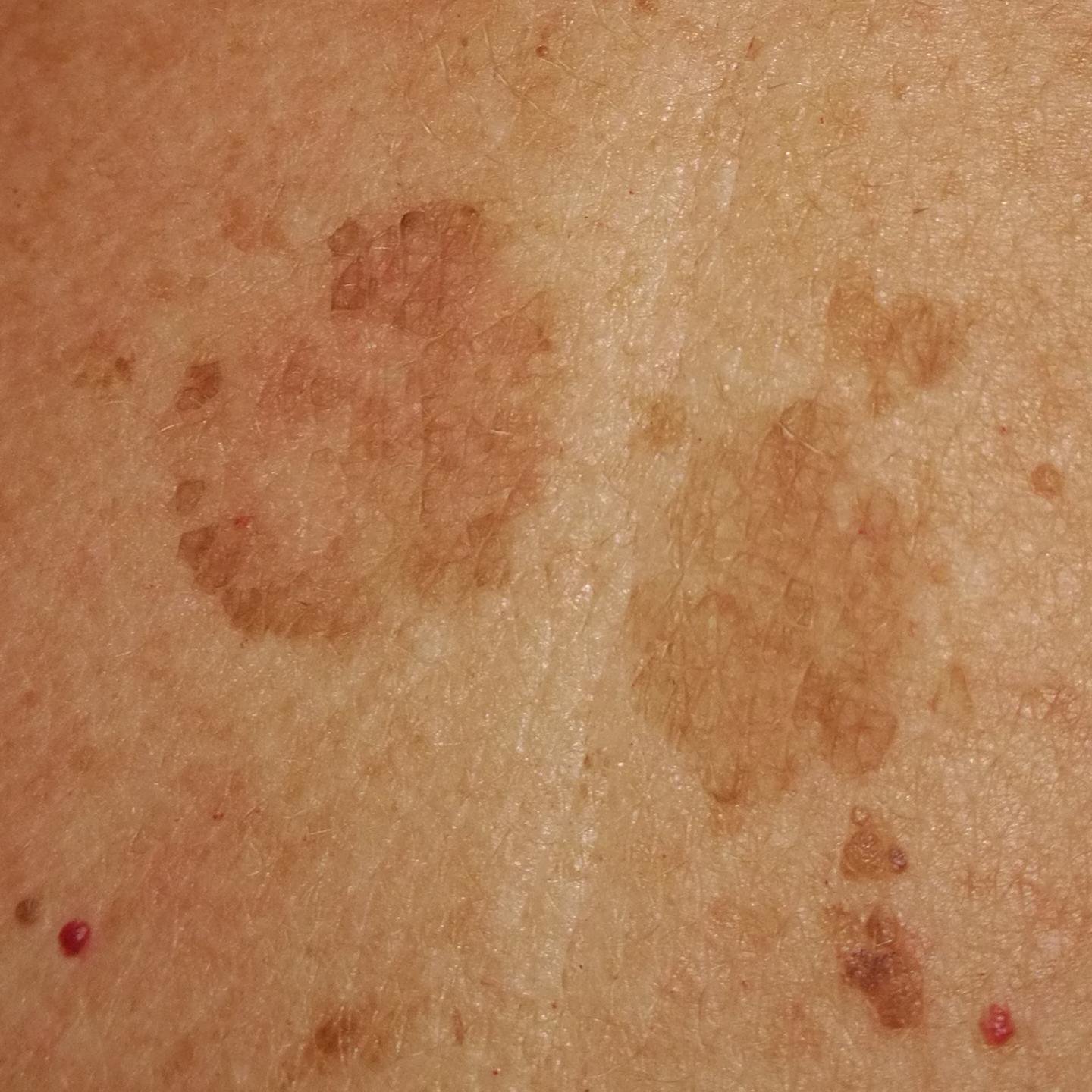Q: Patient demographics?
A: female, age 57
Q: What kind of image is this?
A: smartphone clinical photo
Q: What is the patient's skin type?
A: II
Q: What are the relevant risk factors?
A: prior malignancy (patient or family), pesticide exposure, prior skin cancer (patient or family)
Q: Lesion size?
A: approx. 3 × 3 mm
Q: What is the diagnosis?
A: seborrheic keratosis (clinical consensus)